A macroscopic clinical photograph of a skin lesion · imaged for a research study, with no referral diagnosis recorded · the patient reports no immunosuppression and no family history of skin cancer · the patient says their skin tans without first burning: 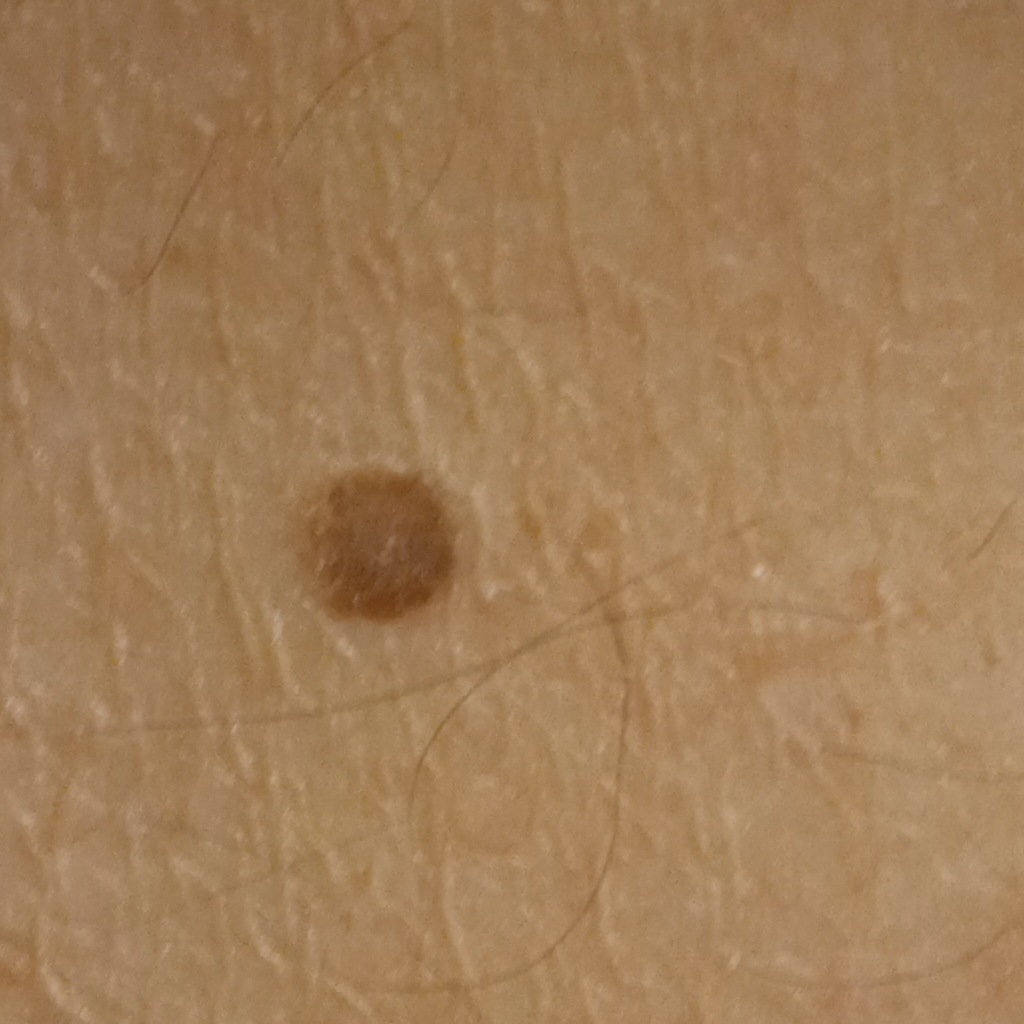Measuring roughly 5.8 mm.
The dermatologists' assessment was a melanocytic nevus.